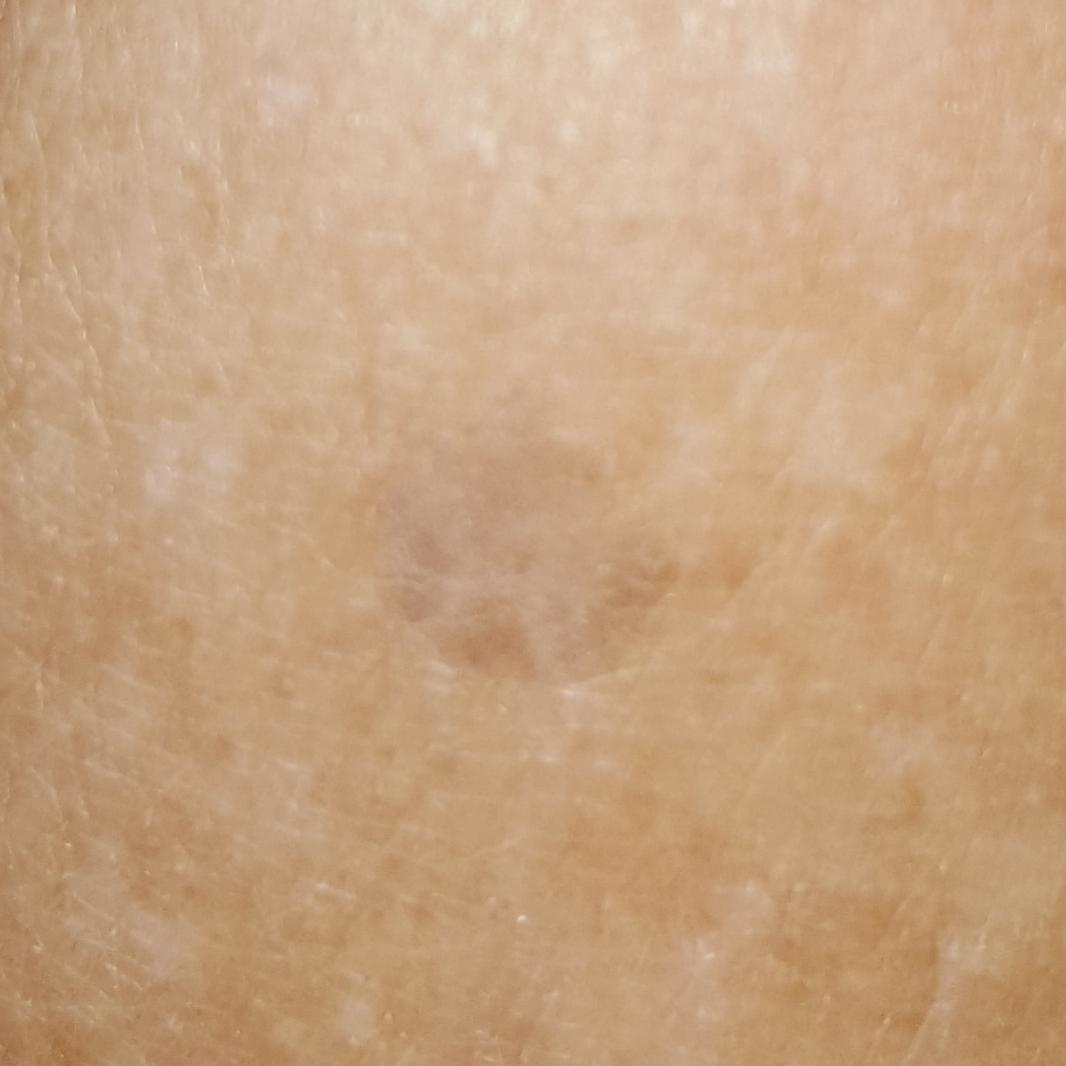impression: seborrheic keratosis (clinical consensus).